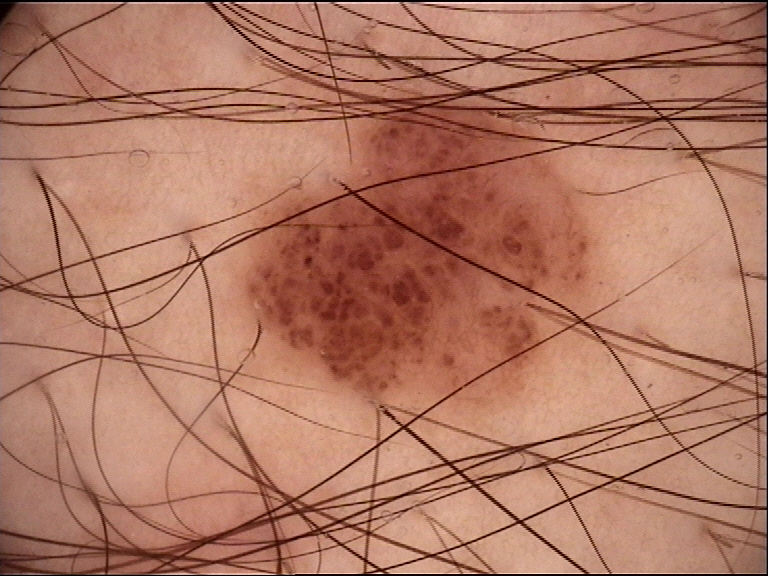Dermoscopy of a skin lesion. Classified as a banal lesion — a junctional nevus.